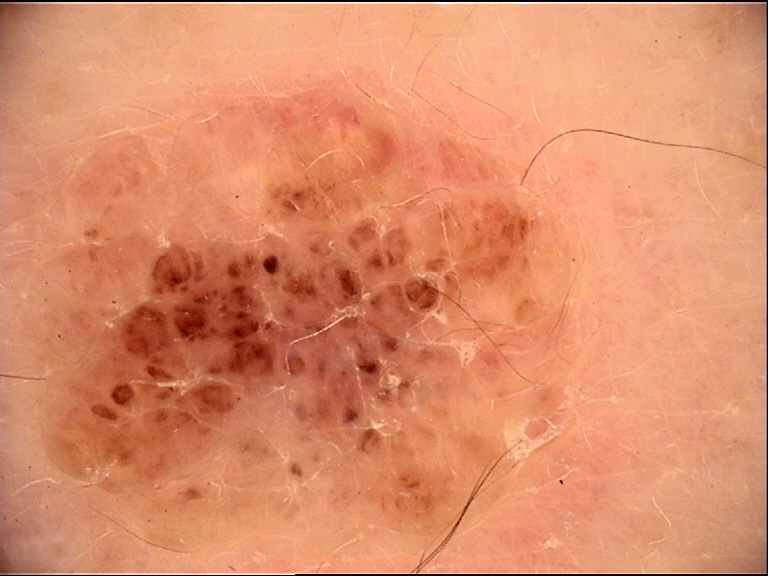Impression:
Diagnosed as a seborrheic keratosis.